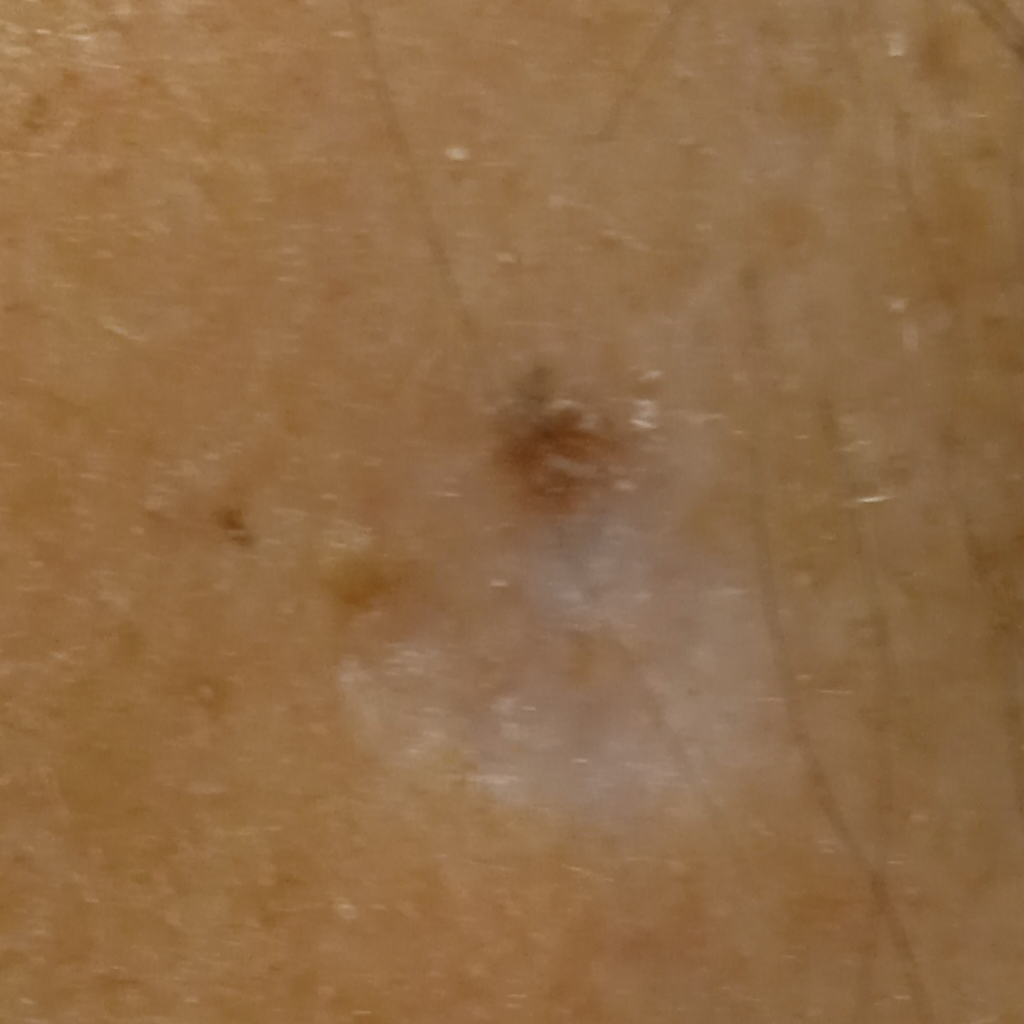| feature | finding |
|---|---|
| diagnosis | basal cell carcinoma (biopsy-proven) |